Present for less than one week · the contributor is a female aged 18–29 · the affected area is the arm, top or side of the foot and leg · the photograph was taken at a distance:
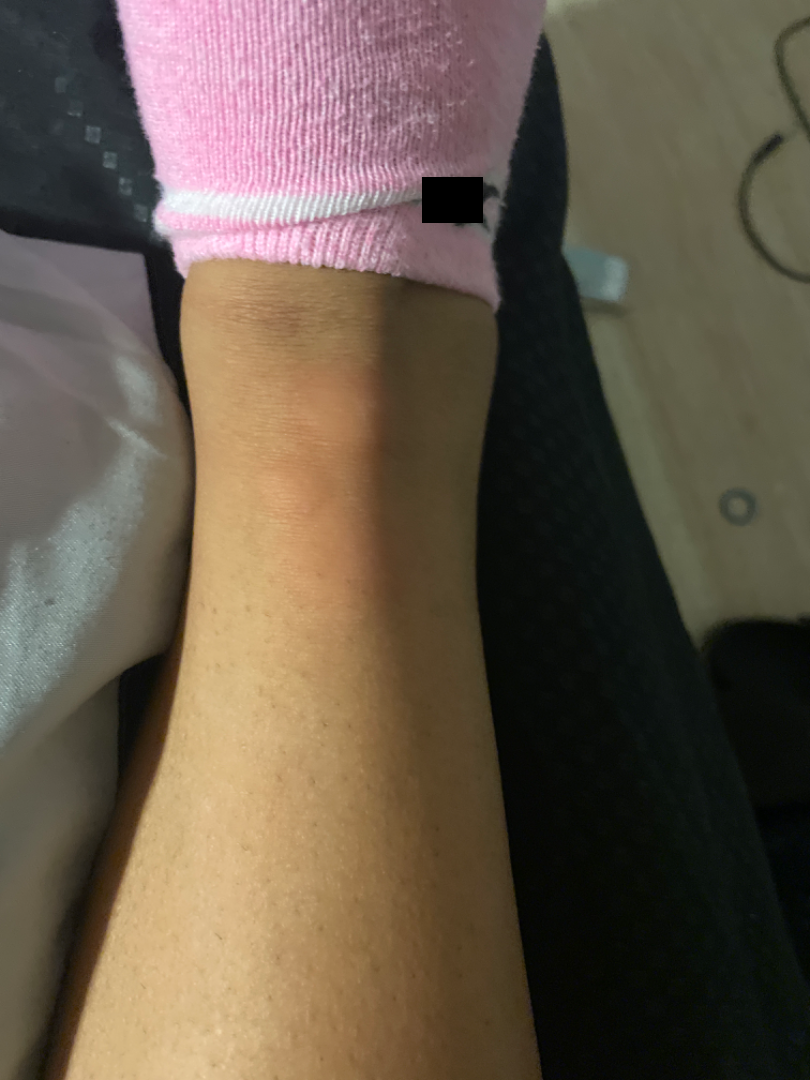Impression:
The condition could not be reliably identified from the image.